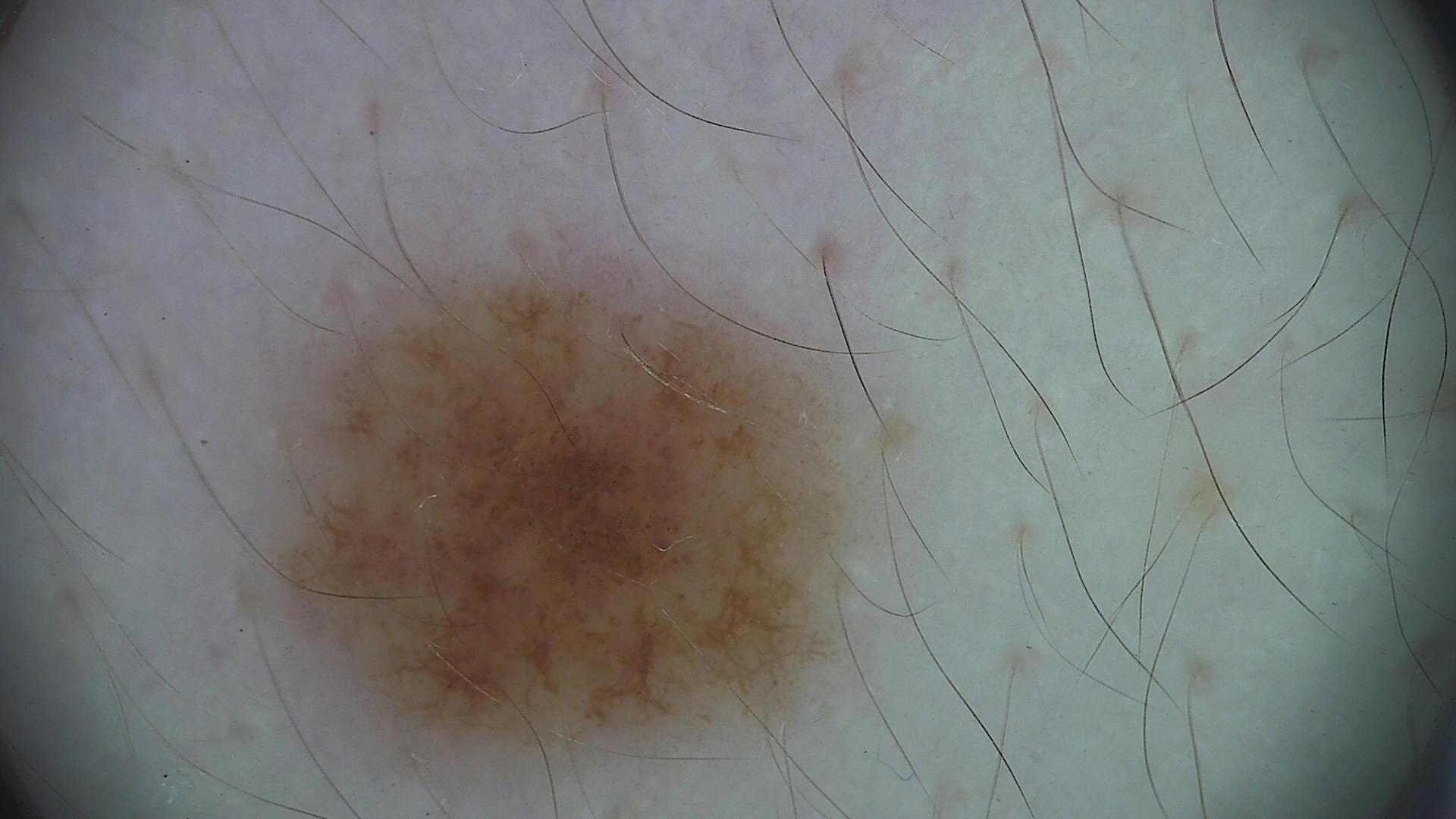{
  "diagnosis": {
    "name": "dysplastic junctional nevus",
    "code": "jd",
    "malignancy": "benign",
    "super_class": "melanocytic",
    "confirmation": "expert consensus"
  }
}